The back of the torso is involved; this is a close-up image: 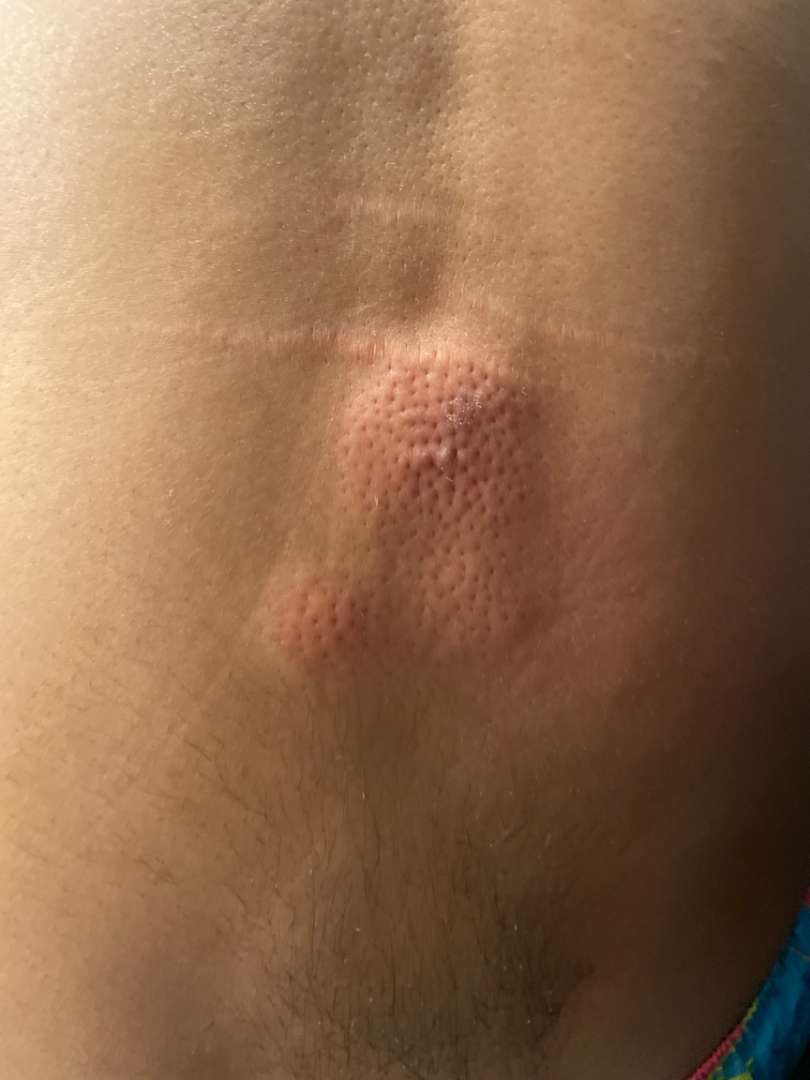assessment = not assessable